A dermoscopic photograph of a skin lesion:
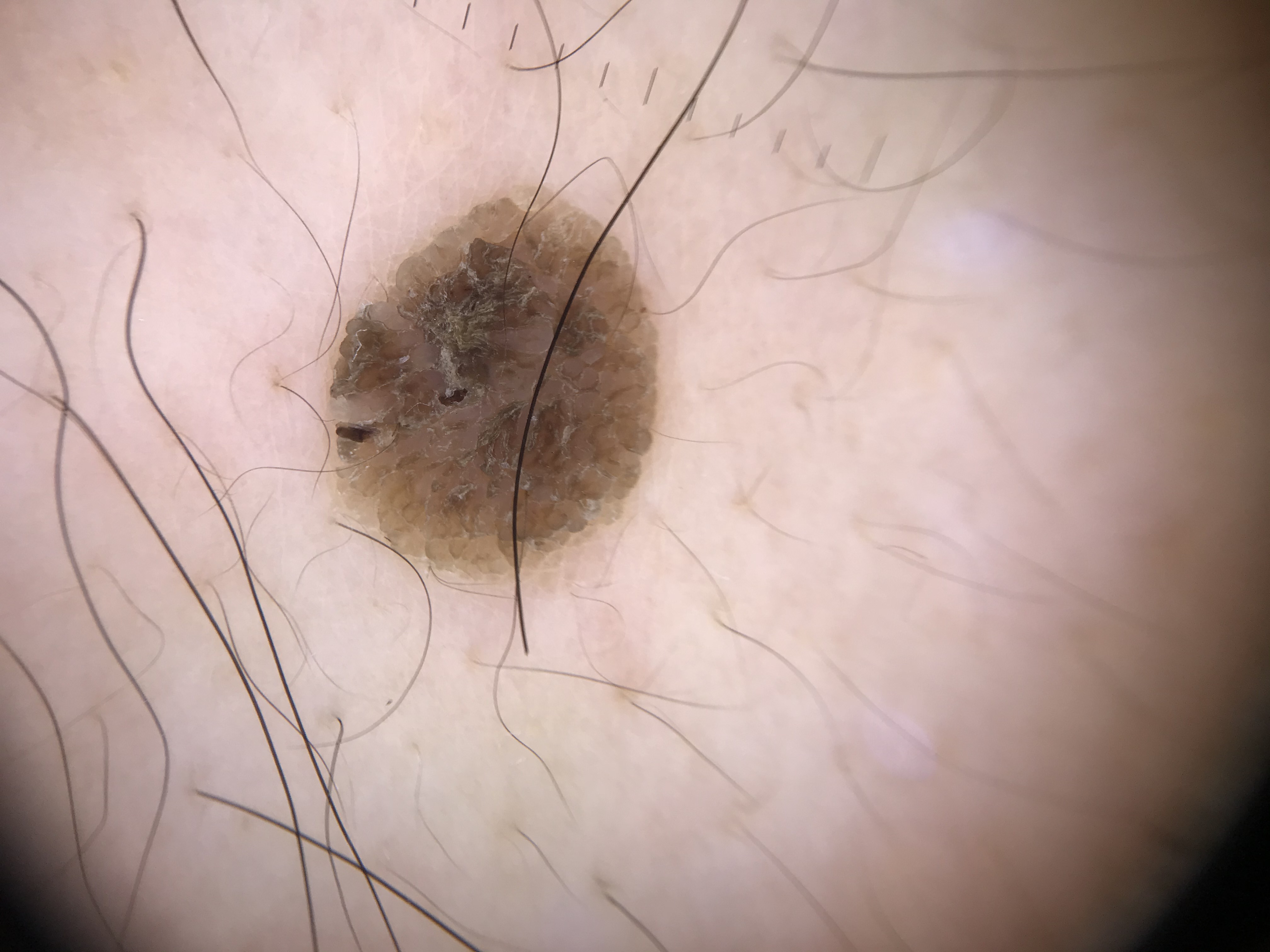{"diagnosis": {"name": "seborrheic keratosis", "code": "sk", "malignancy": "benign", "super_class": "non-melanocytic", "confirmation": "expert consensus"}}